A dermoscopic photograph of a skin lesion:
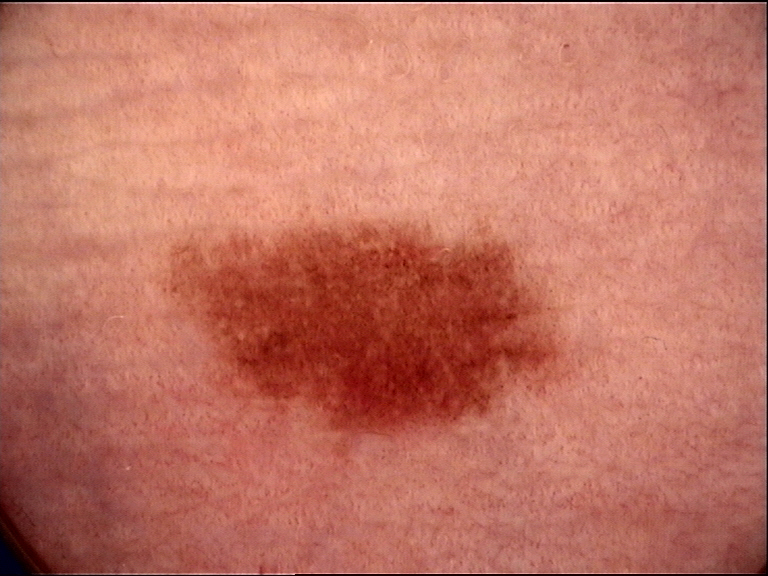The diagnosis was a dysplastic junctional nevus.